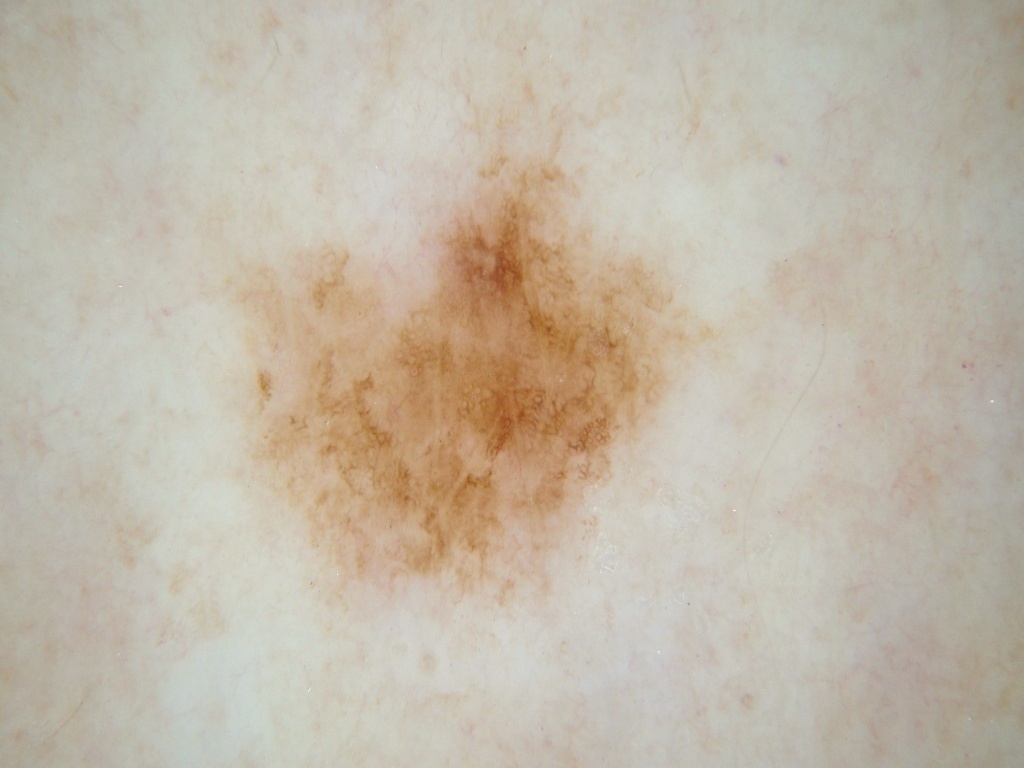subject = female, in their mid- to late 60s
imaging = dermoscopy
features = pigment network
extent = moderate
lesion bbox = (207, 95, 719, 641)
diagnosis = a melanocytic nevus